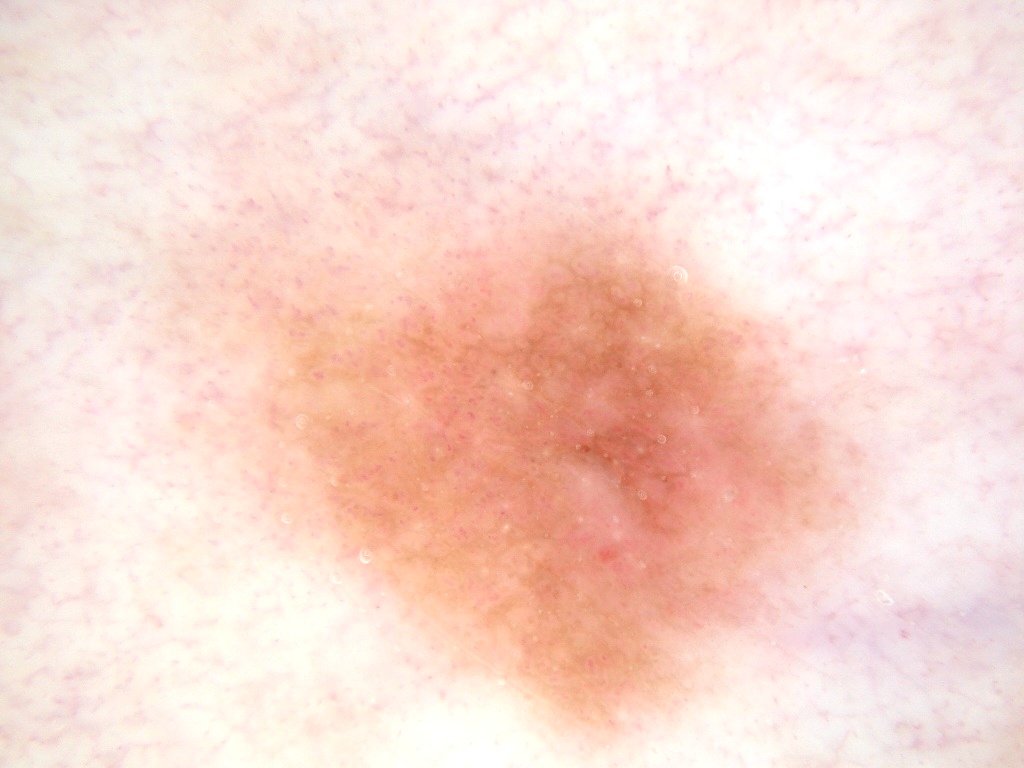This is a dermoscopic photograph of a skin lesion.
A female subject, aged around 50.
With coordinates (x1, y1, x2, y2), the lesion occupies the region 125/135/885/762.
The dermoscopic pattern shows milia-like cysts and pigment network.
The clinical diagnosis was a melanocytic nevus.